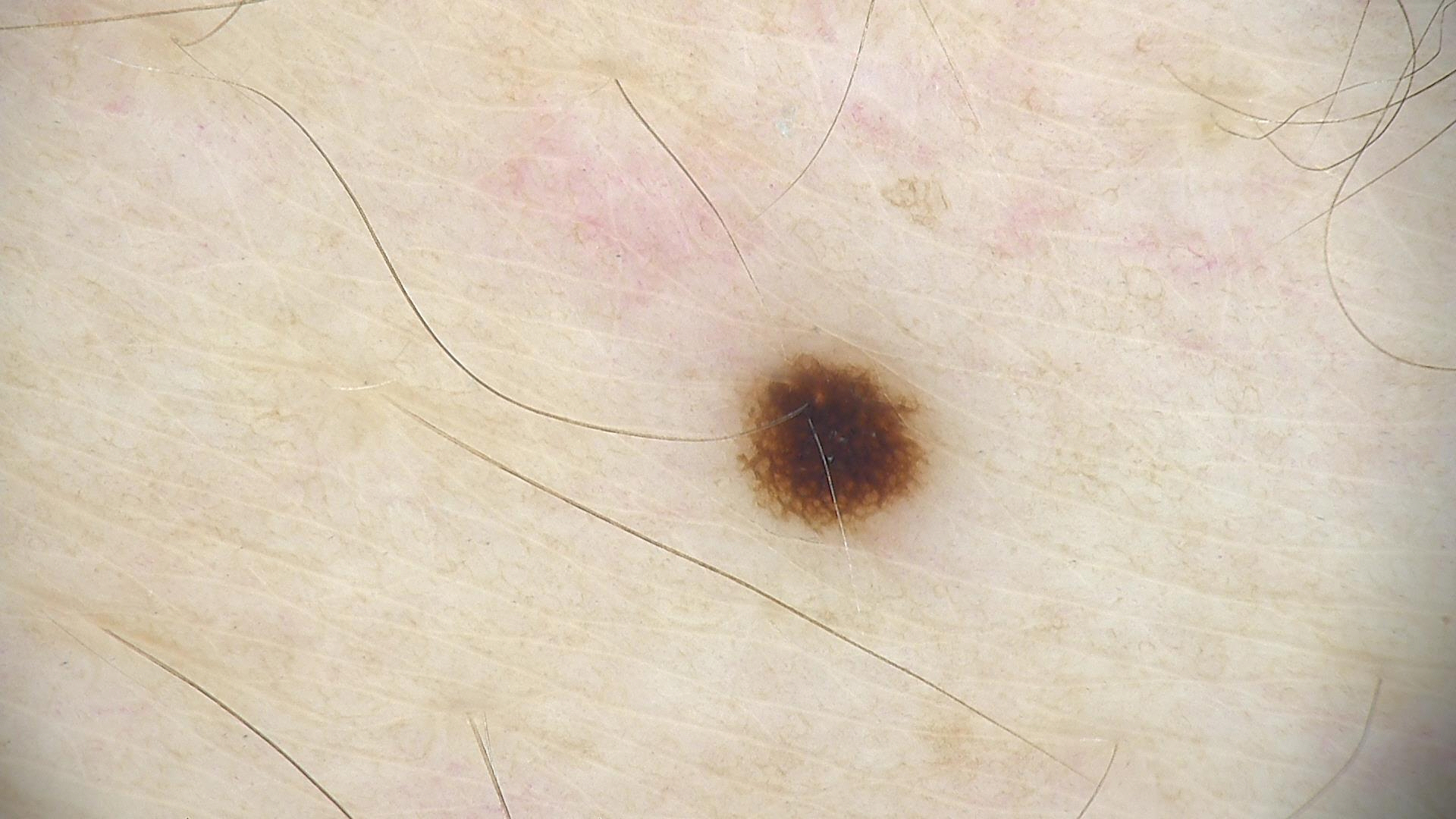Labeled as a dysplastic junctional nevus.